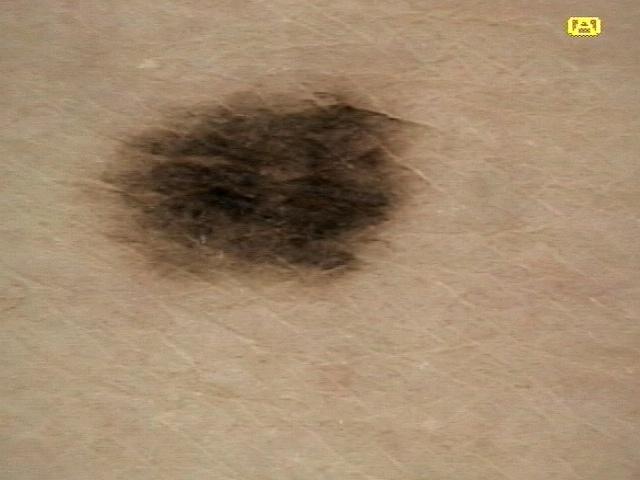A dermoscopic photograph of a skin lesion.
The chart notes a prior melanoma but no melanoma in first-degree relatives.
The patient is Fitzpatrick phototype II.
A female patient aged 58 to 62.
The lesion is on the trunk (the posterior trunk).
Confirmed on histopathology as a lesion of melanocytic lineage — a nevus.